The condition has been present for less than one week. The lesion is described as raised or bumpy. The affected area is the head or neck. This image was taken at an angle — 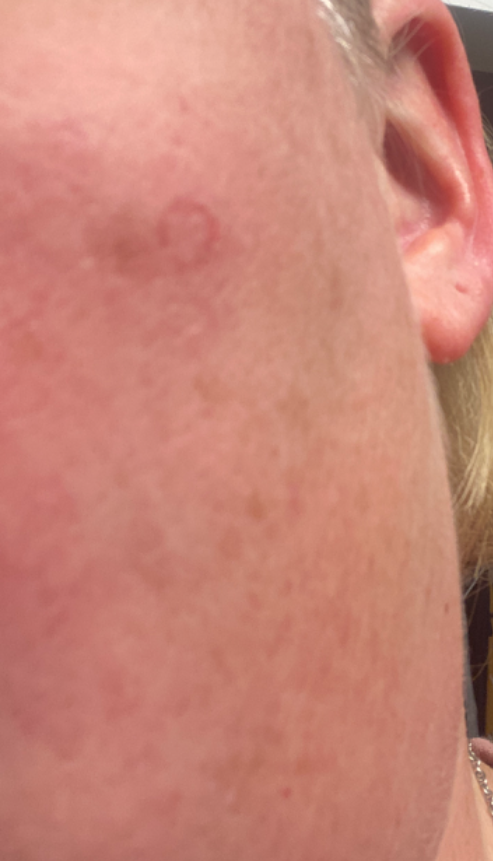Diagnostic features were not clearly distinguishable in this photograph.